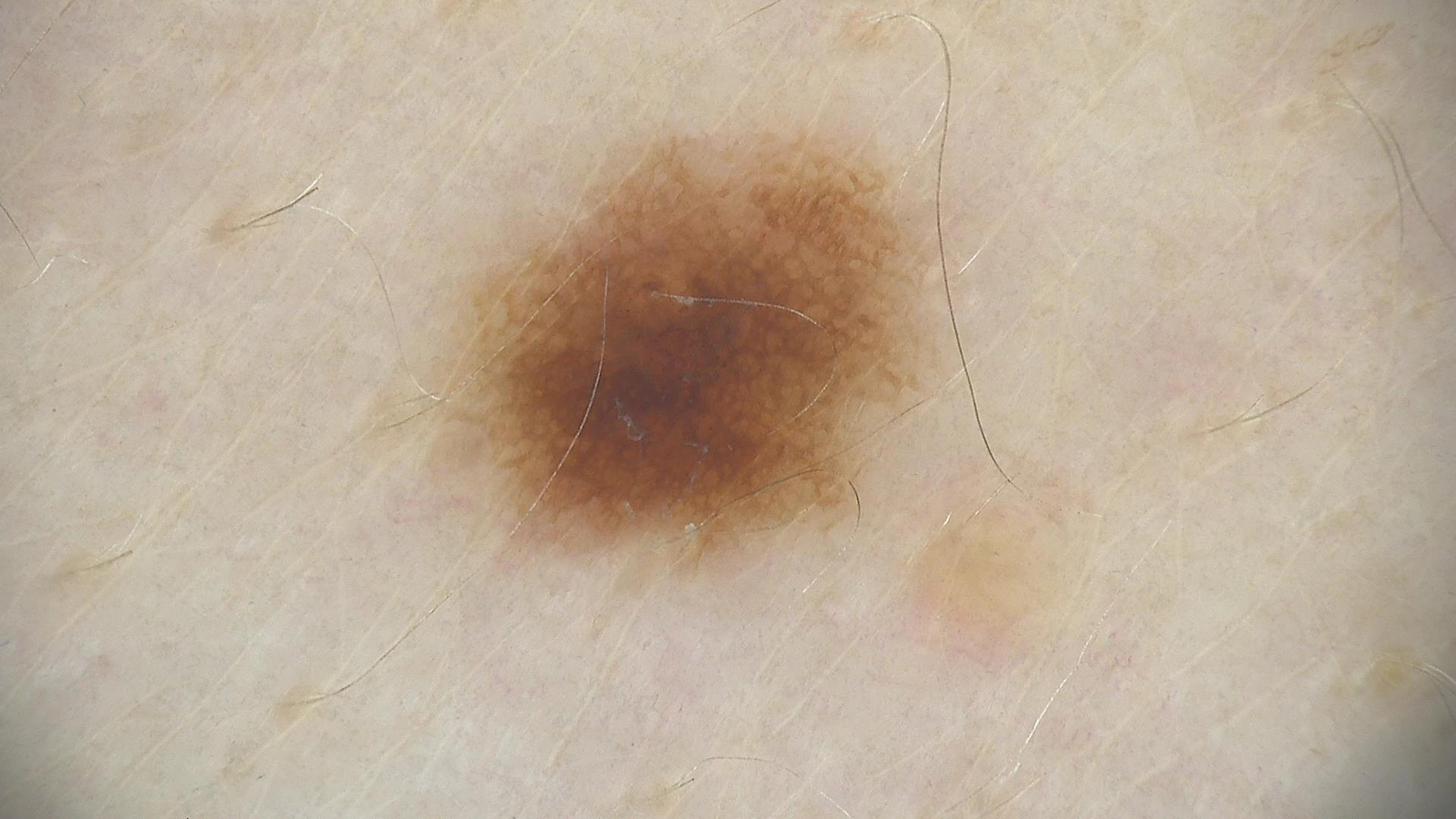A dermoscopic photograph of a skin lesion. Consistent with a dysplastic junctional nevus.